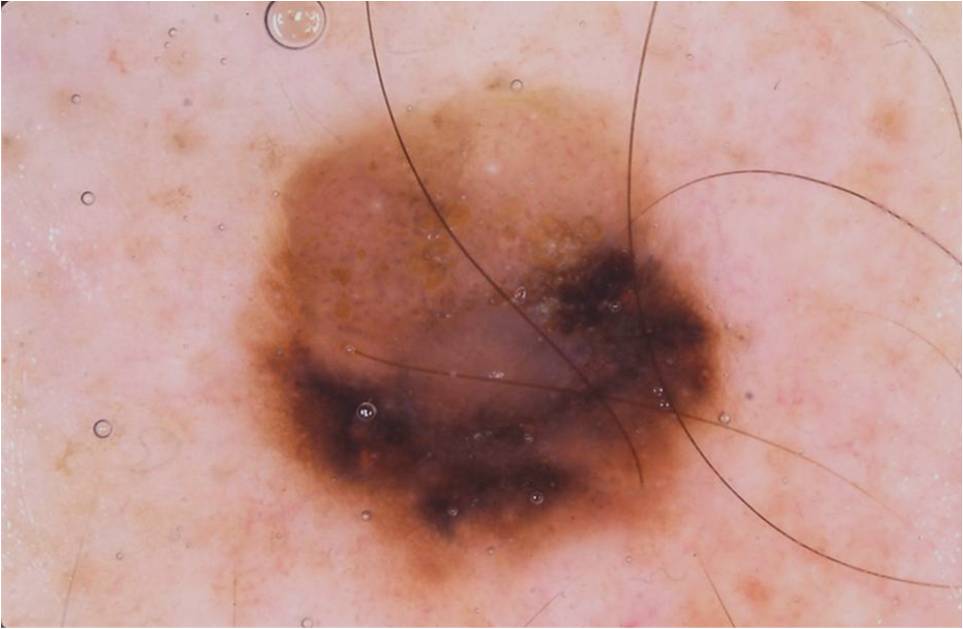patient = male, roughly 60 years of age | imaging = dermoscopy of a skin lesion | bounding box = 230, 74, 754, 604 | dermoscopic features = pigment network; absent: milia-like cysts, streaks, negative network, and globules | size = ~33% of the field | diagnostic label = a melanoma, a malignant lesion.